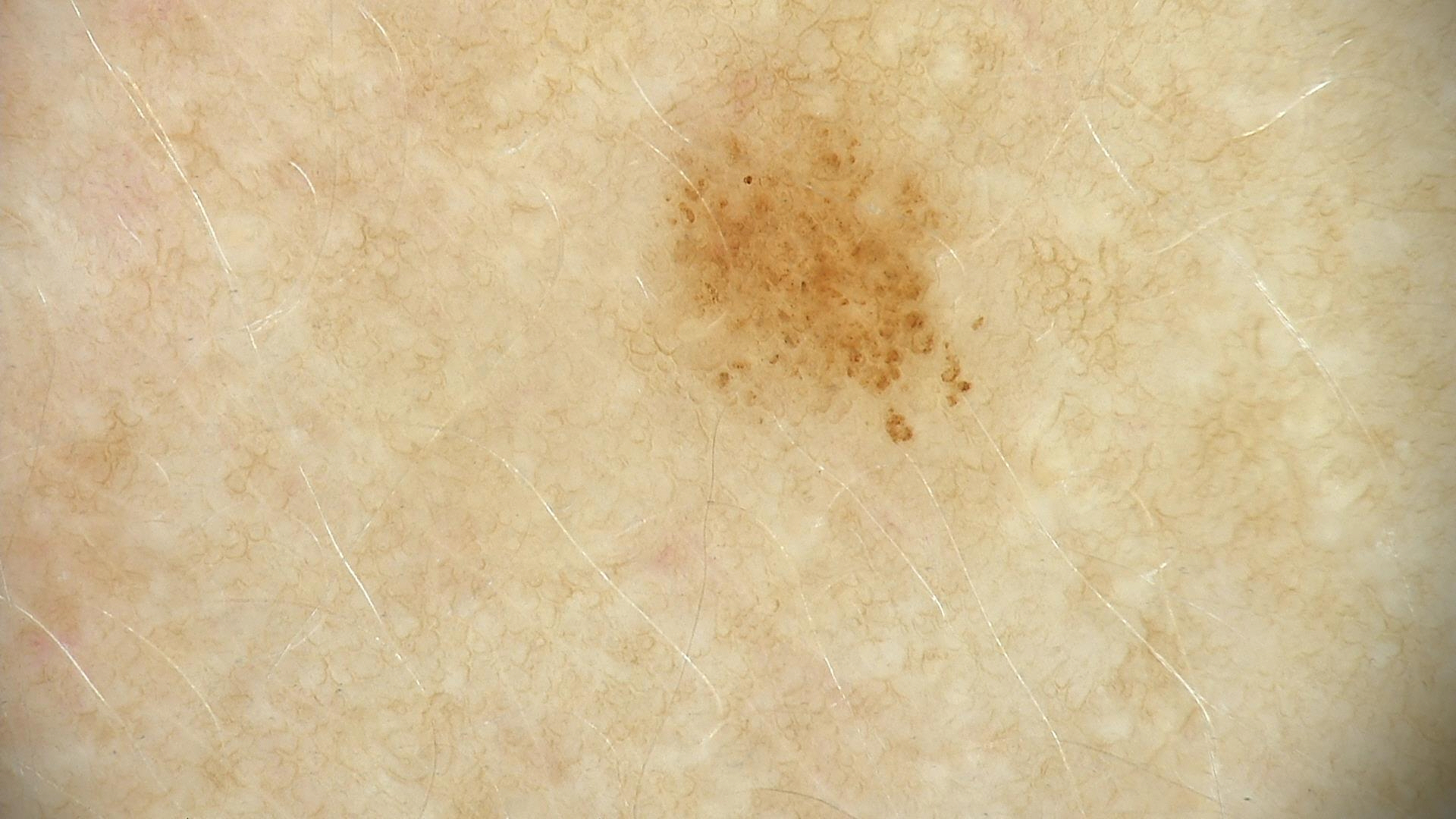Summary: A dermoscopy image of a single skin lesion. Impression: Labeled as a benign lesion — a dysplastic junctional nevus.